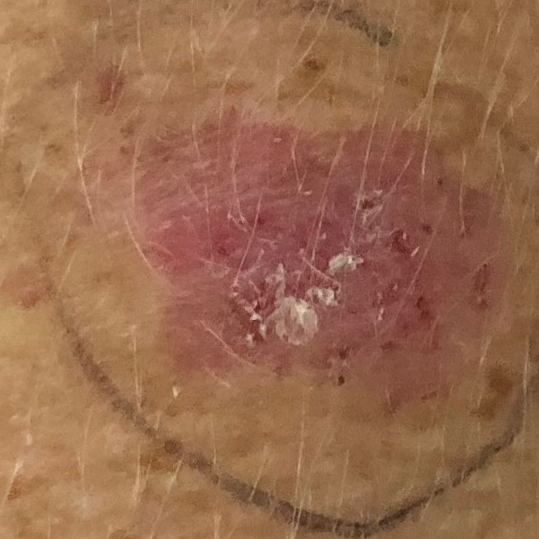<case>
<skin_type>I</skin_type>
<patient>
<age>42</age>
<gender>female</gender>
</patient>
<lesion_size>
<diameter_1_mm>20.0</diameter_1_mm>
<diameter_2_mm>12.0</diameter_2_mm>
</lesion_size>
<symptoms>
<present>elevation, itching</present>
</symptoms>
<diagnosis>
<name>basal cell carcinoma</name>
<code>BCC</code>
<malignancy>malignant</malignancy>
<confirmation>histopathology</confirmation>
</diagnosis>
</case>